The photograph is a close-up of the affected area: 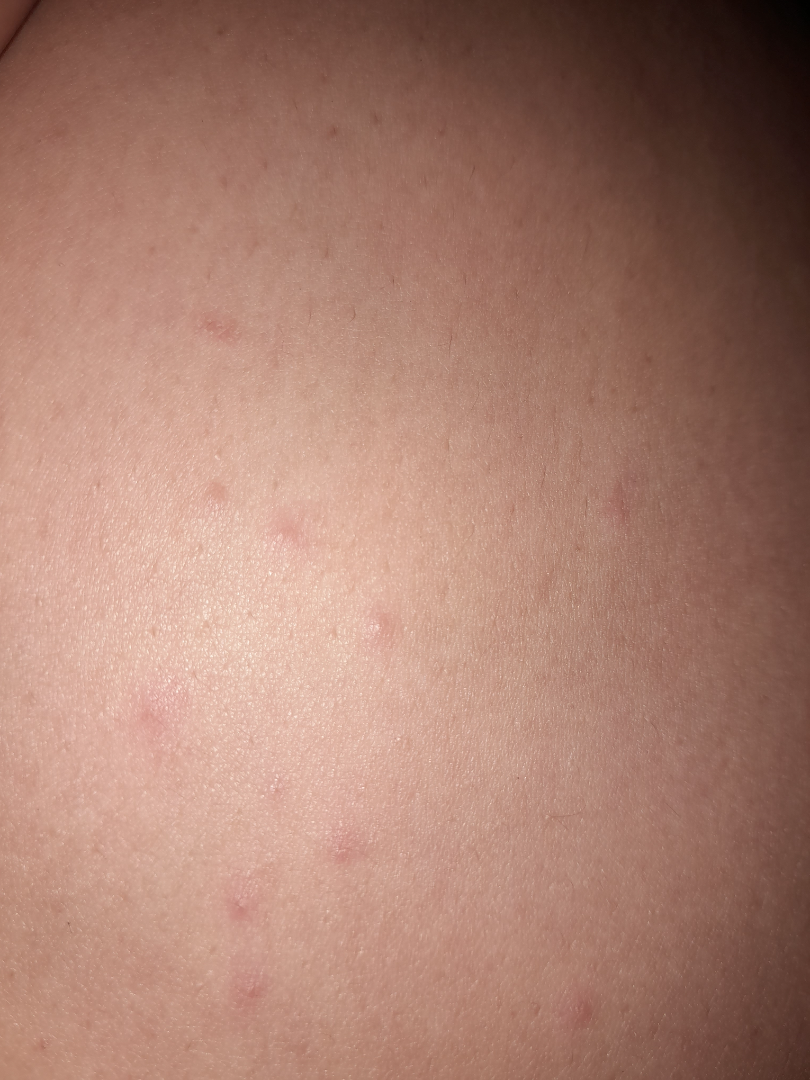diagnostic considerations — reviewed remotely by one dermatologist: favoring Folliculitis; also consider Eczema; an alternative is Molluscum Contagiosum